A dermatoscopic image of a skin lesion.
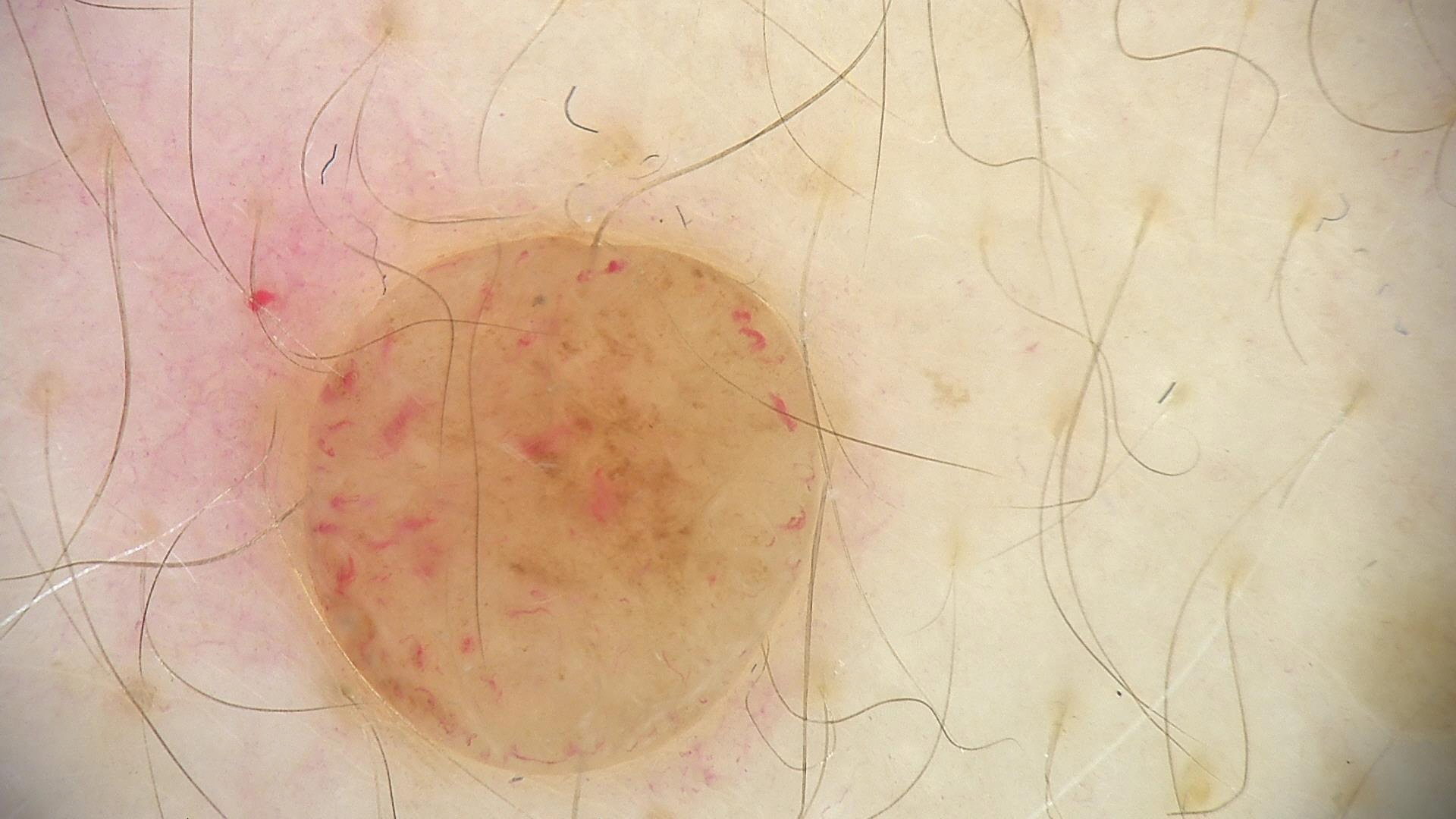lesion type: banal | class: dermal nevus (expert consensus).